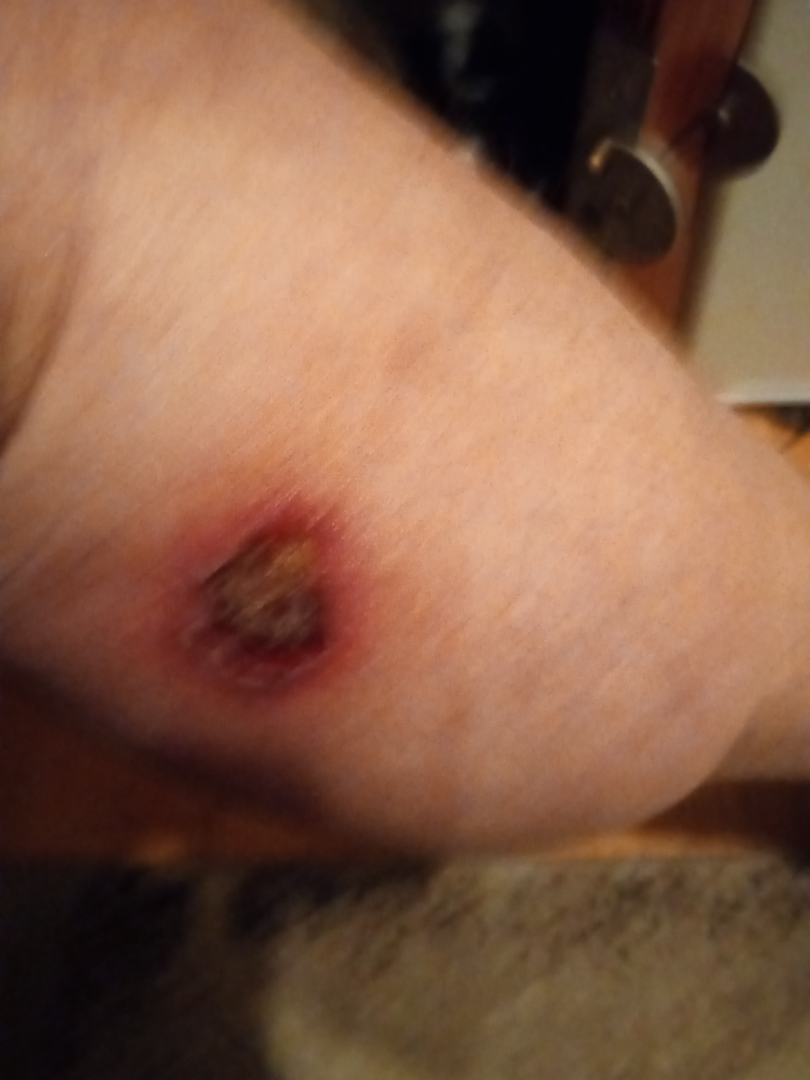Impression:
No differential diagnosis could be assigned on photographic review.